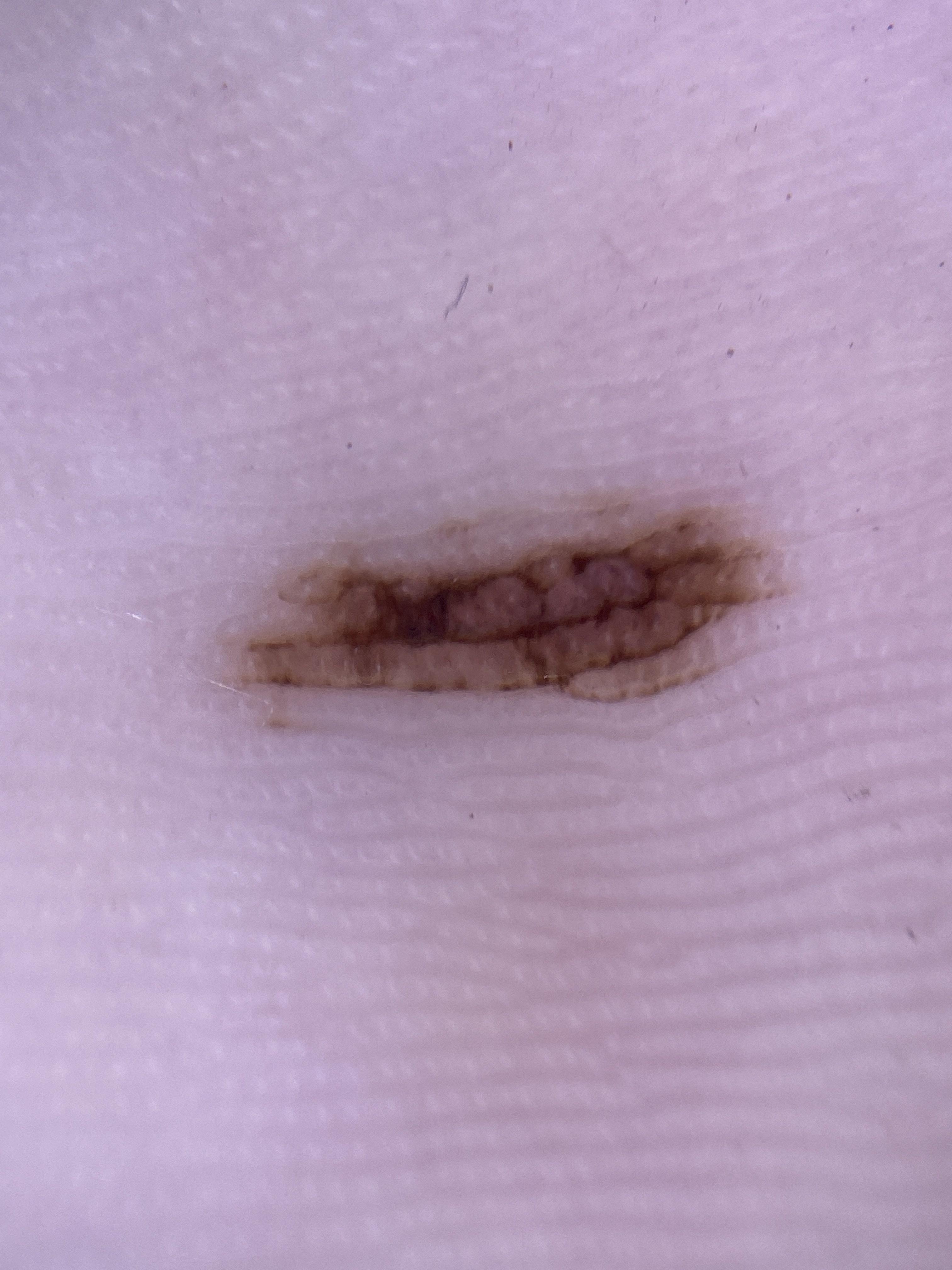| key | value |
|---|---|
| diagnosis | Nevus (biopsy-proven) |